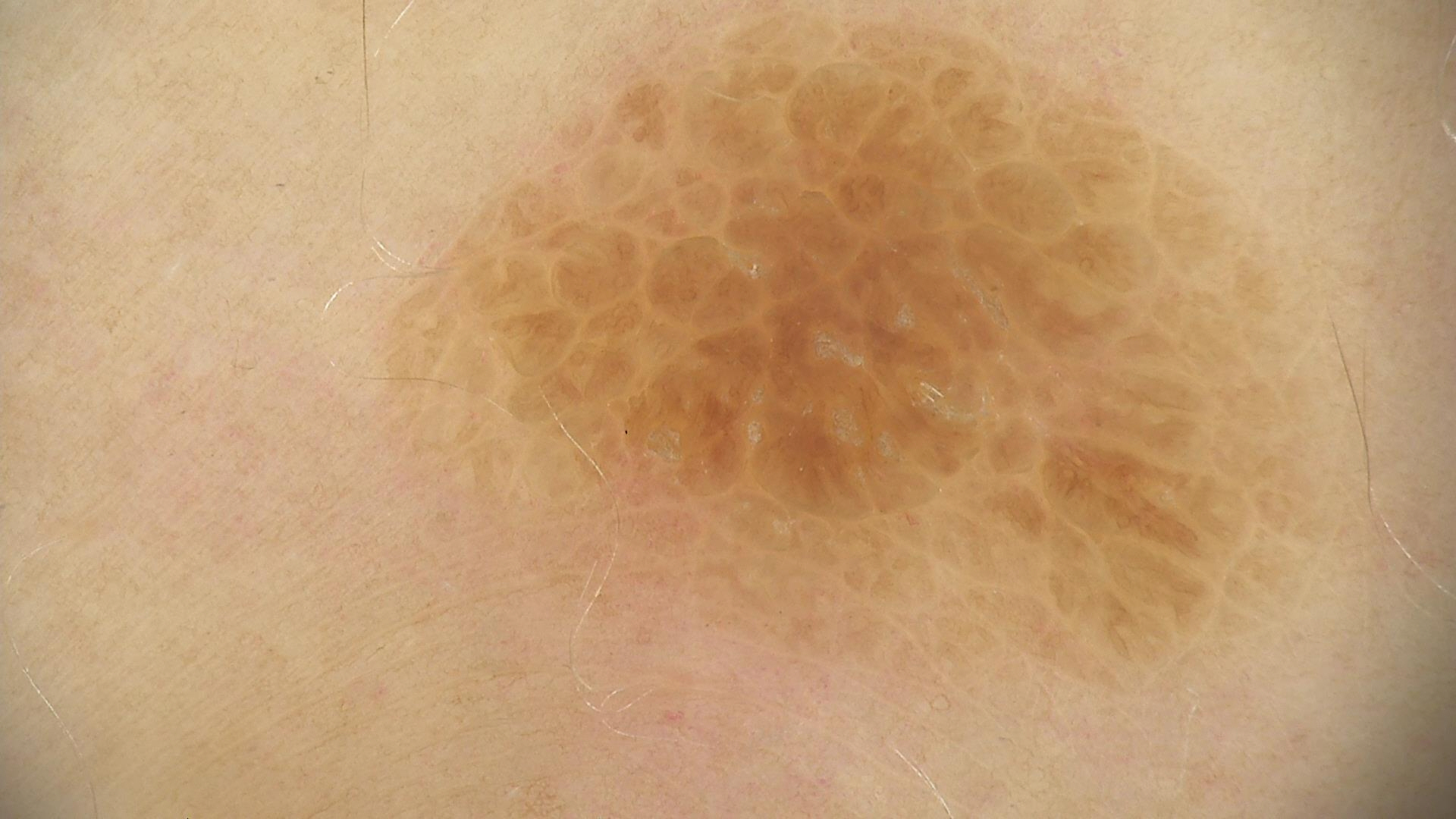diagnostic label: seborrheic keratosis (expert consensus).